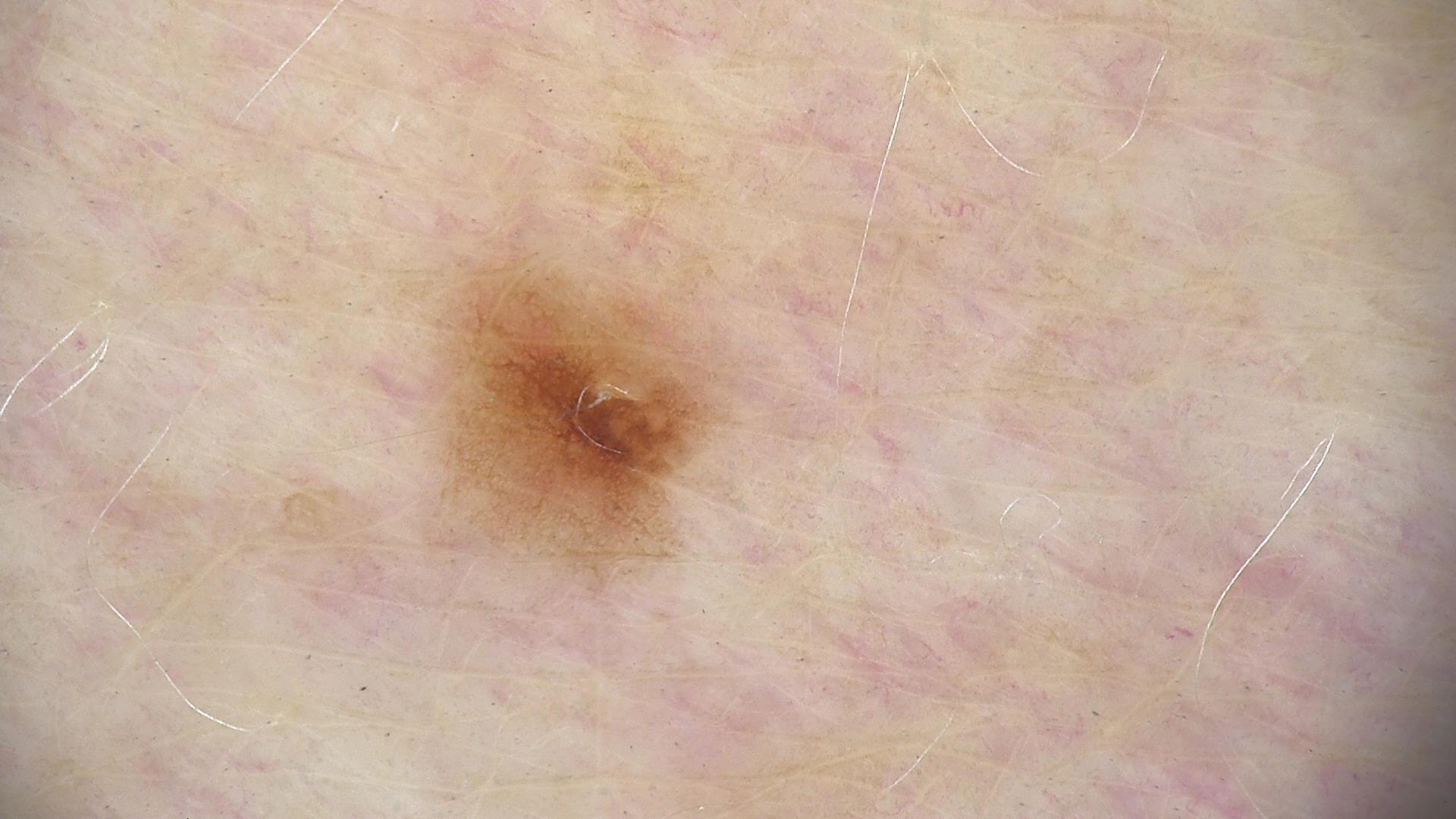assessment — dysplastic junctional nevus (expert consensus)